A subject 79 years old. A clinical photo of a skin lesion taken with a smartphone — 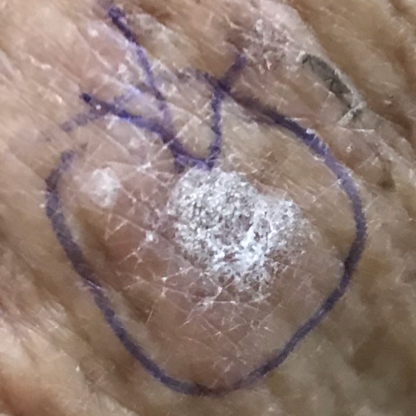anatomic site: an arm; symptoms: growth, bleeding, itching, change in appearance; assessment: actinic keratosis (clinical consensus).